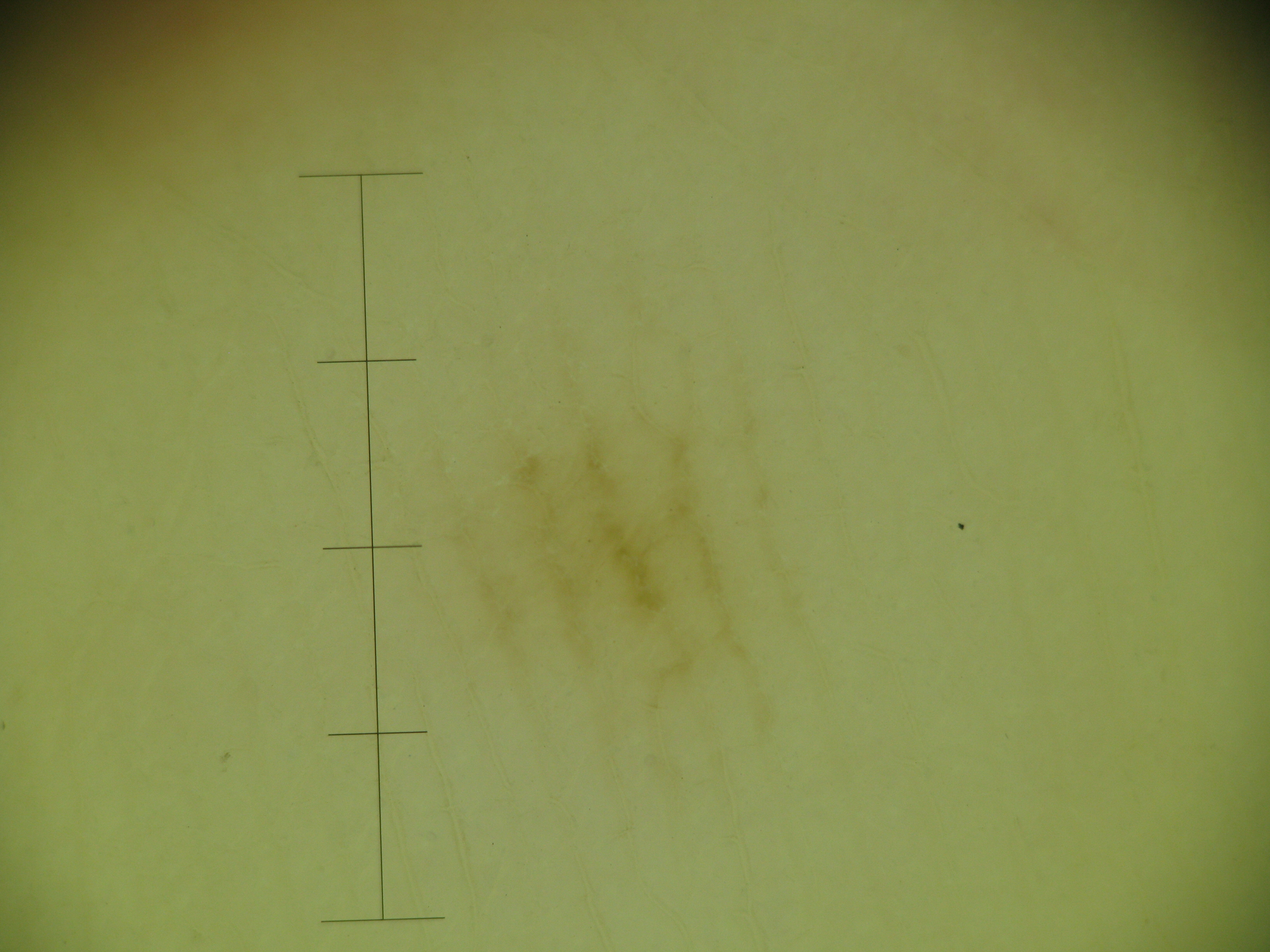  diagnosis:
    name: acral junctional nevus
    code: ajb
    malignancy: benign
    super_class: melanocytic
    confirmation: expert consensus